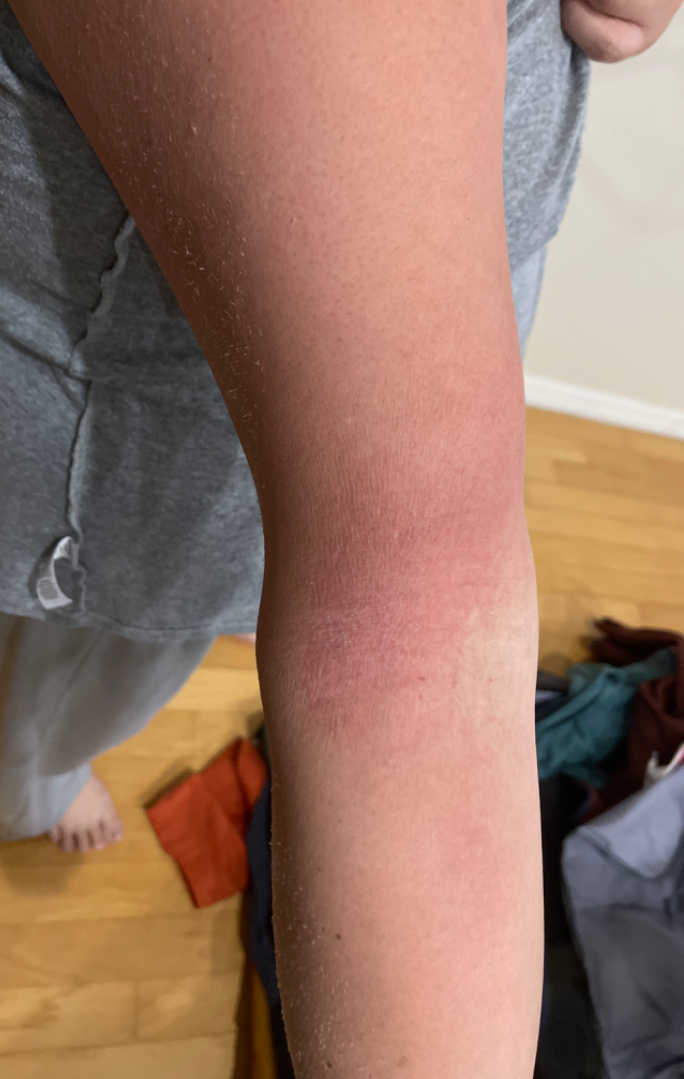<dermatology_case>
  <shot_type>at a distance</shot_type>
  <patient>female, age 30–39</patient>
  <body_site>front of the torso, arm, leg</body_site>
  <differential>
    <leading>Eczema</leading>
    <considered>Xerosis</considered>
    <unlikely>Lichen Simplex Chronicus</unlikely>
  </differential>
</dermatology_case>